The patient reported no systemic symptoms. The lesion is described as flat and raised or bumpy. The patient considered this a pigmentary problem. Reported duration is more than five years. Close-up view. The leg is involved. Skin tone: Fitzpatrick phototype IV. Reported lesion symptoms include darkening and itching — 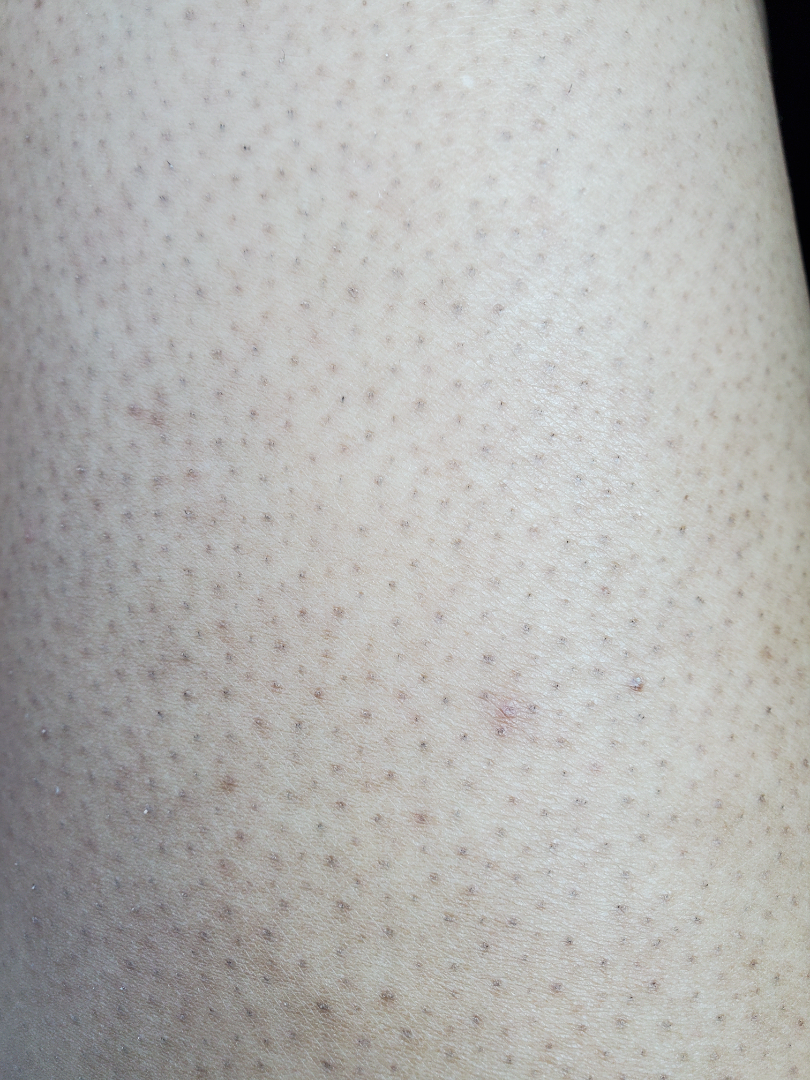Q: What conditions are considered?
A: consistent with Folliculitis